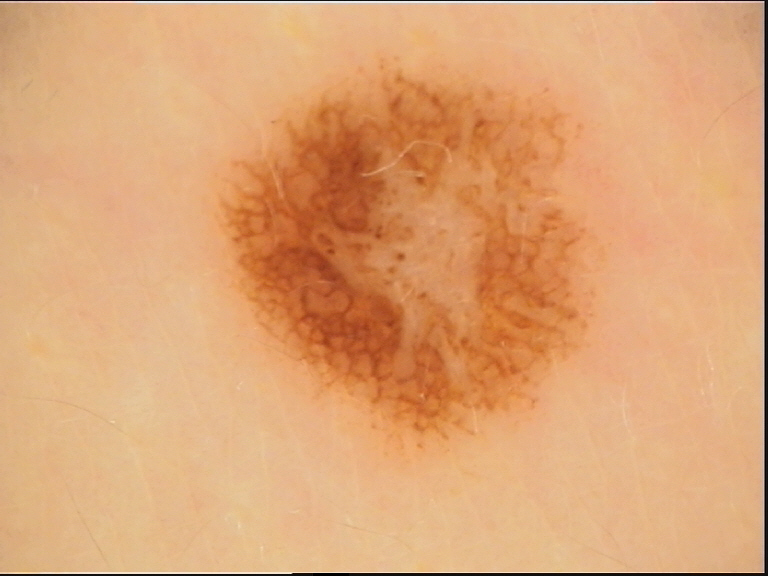lesion type: fibro-histiocytic
assessment: dermatofibroma (expert consensus)